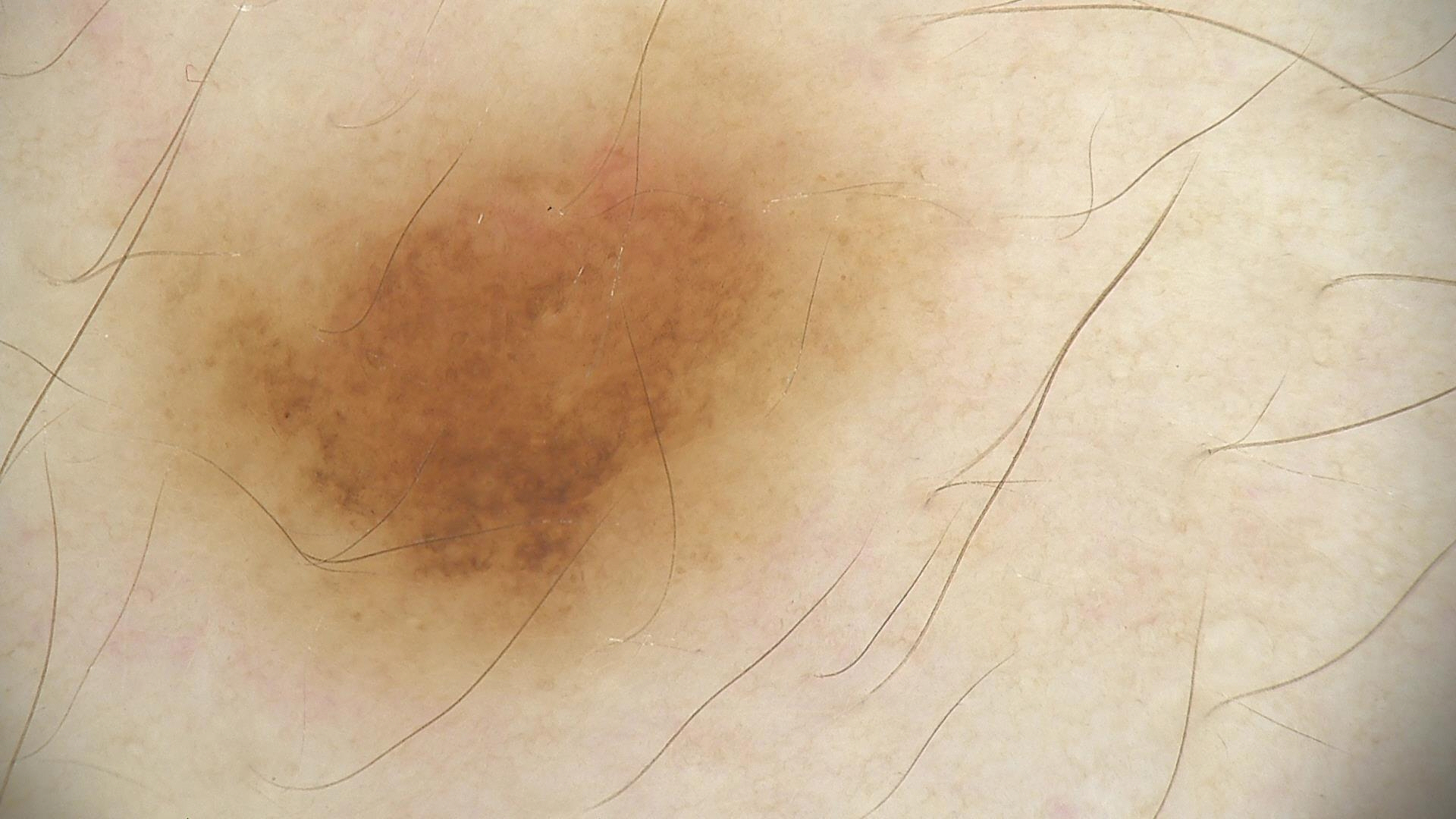class: dysplastic junctional nevus (expert consensus)